Dermoscopy of a skin lesion.
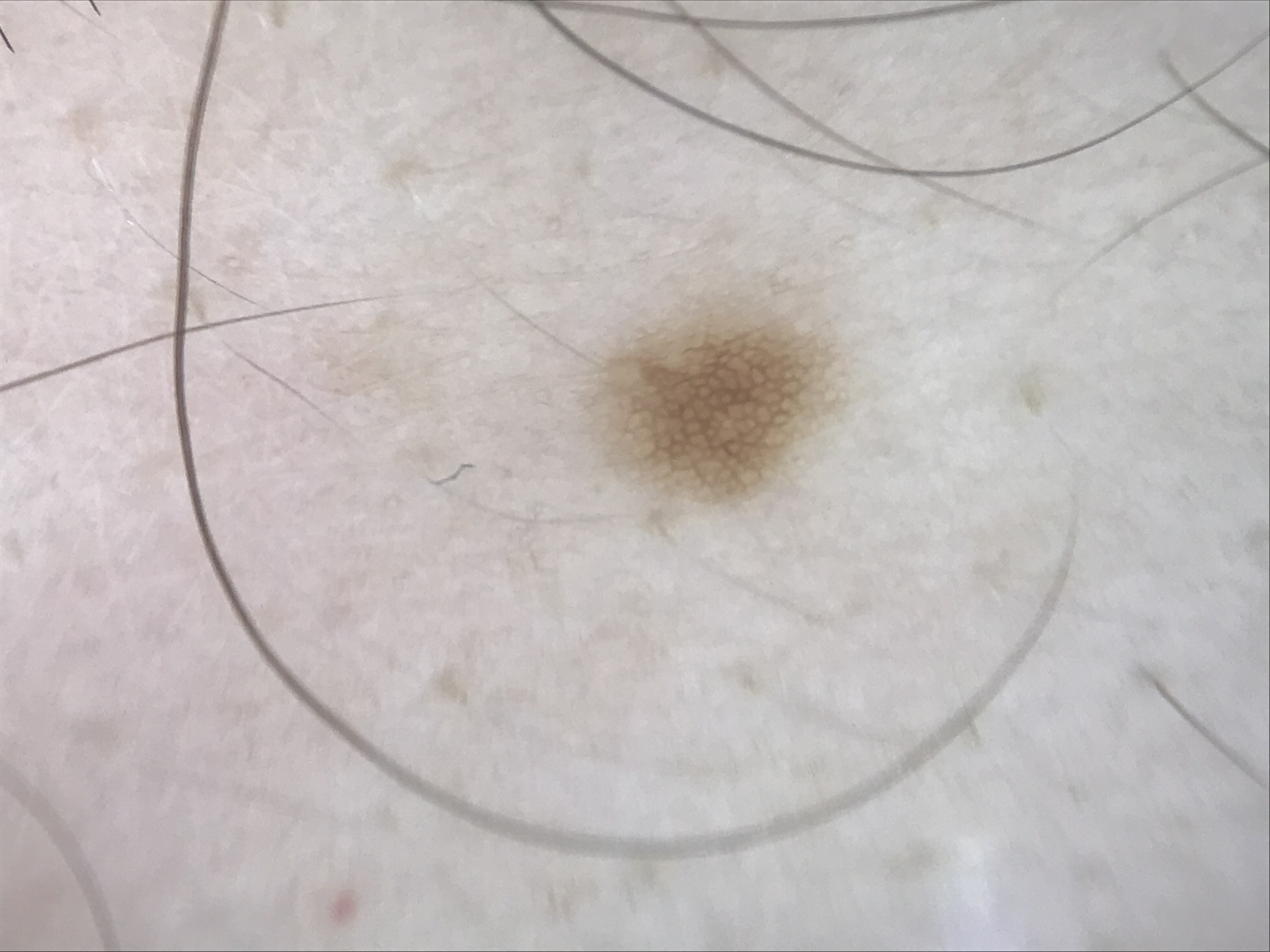Case:
- subtype: banal
- diagnostic label: junctional nevus (expert consensus)